A dermoscopic image of a skin lesion.
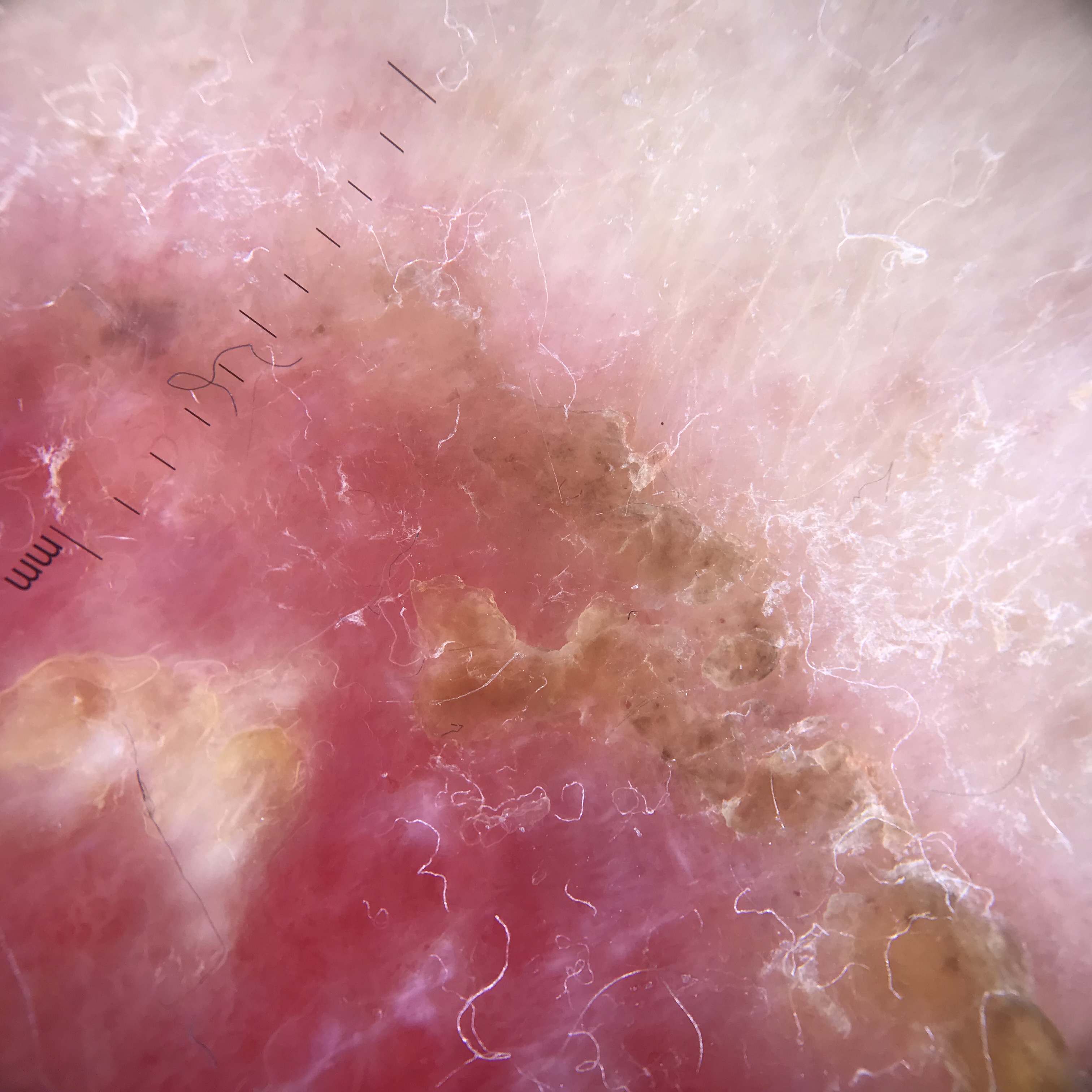lesion type: keratinocytic
diagnosis: Bowen's disease (biopsy-proven)